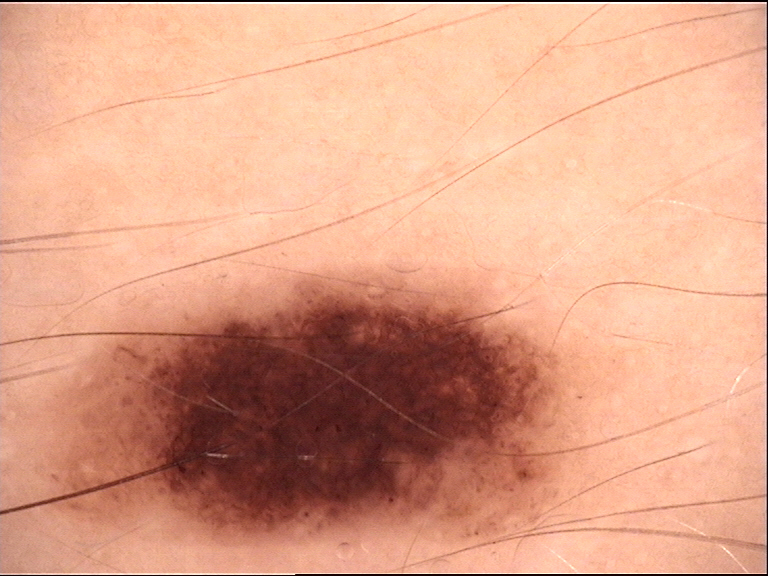label: dysplastic junctional nevus (expert consensus).